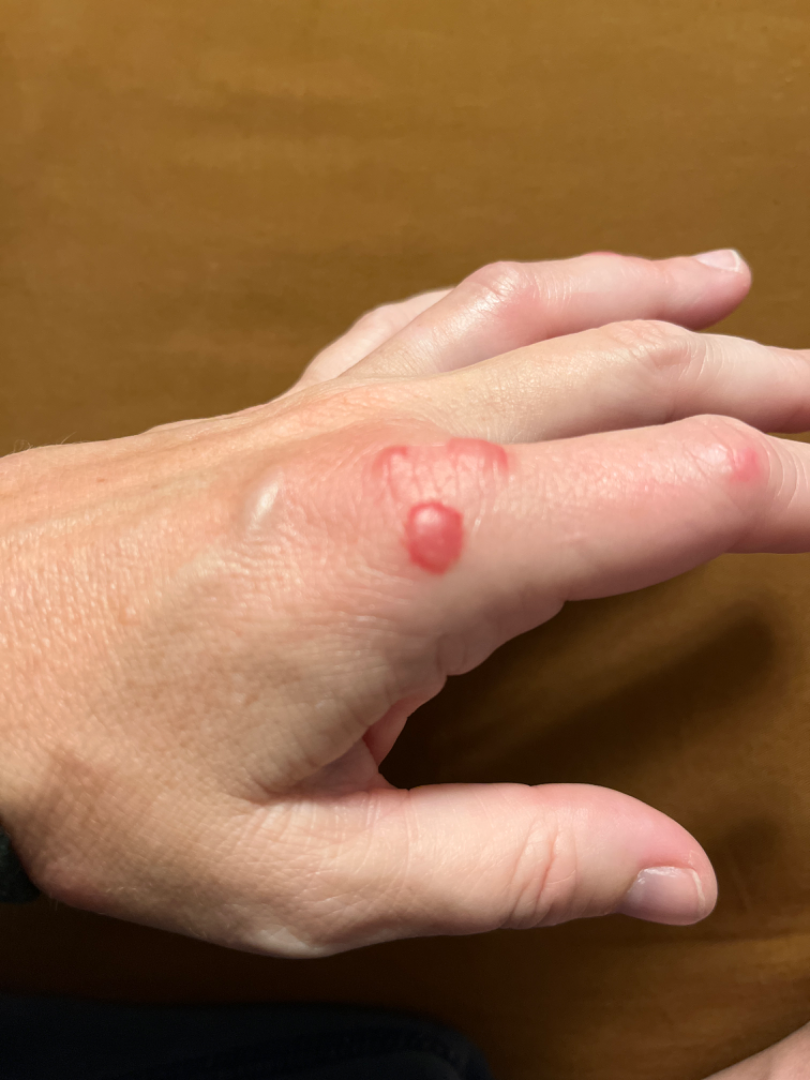Notes:
– assessment — ungradable on photographic review
– described texture — fluid-filled
– patient-reported symptoms — itching, pain and burning
– symptom duration — about one day
– systemic symptoms — fatigue and joint pain
– framing — at an angle